A skin lesion imaged with contact-polarized dermoscopy.
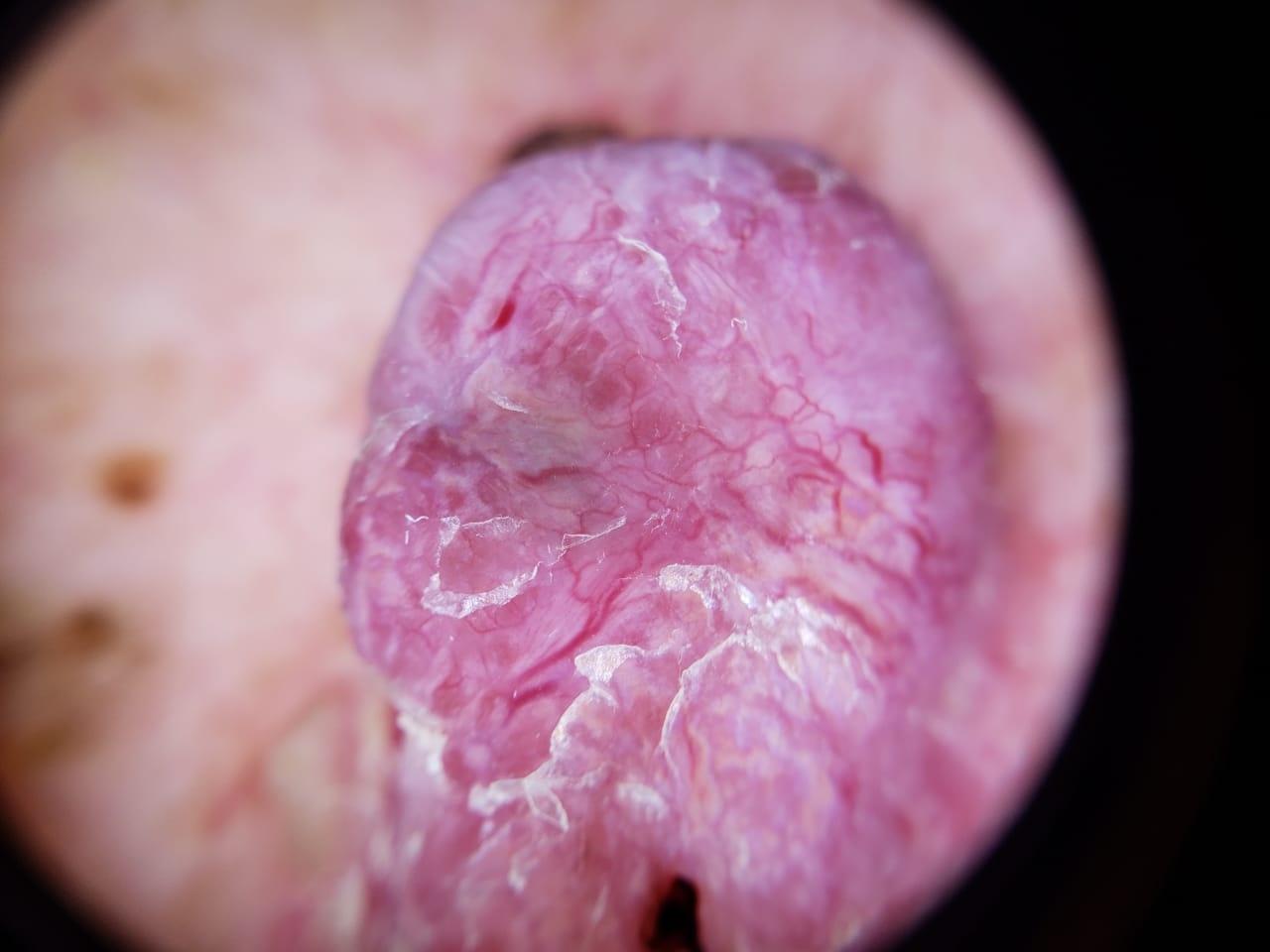The lesion is on the trunk. The biopsy diagnosis was a melanoma.